A dermatoscopic image of a skin lesion.
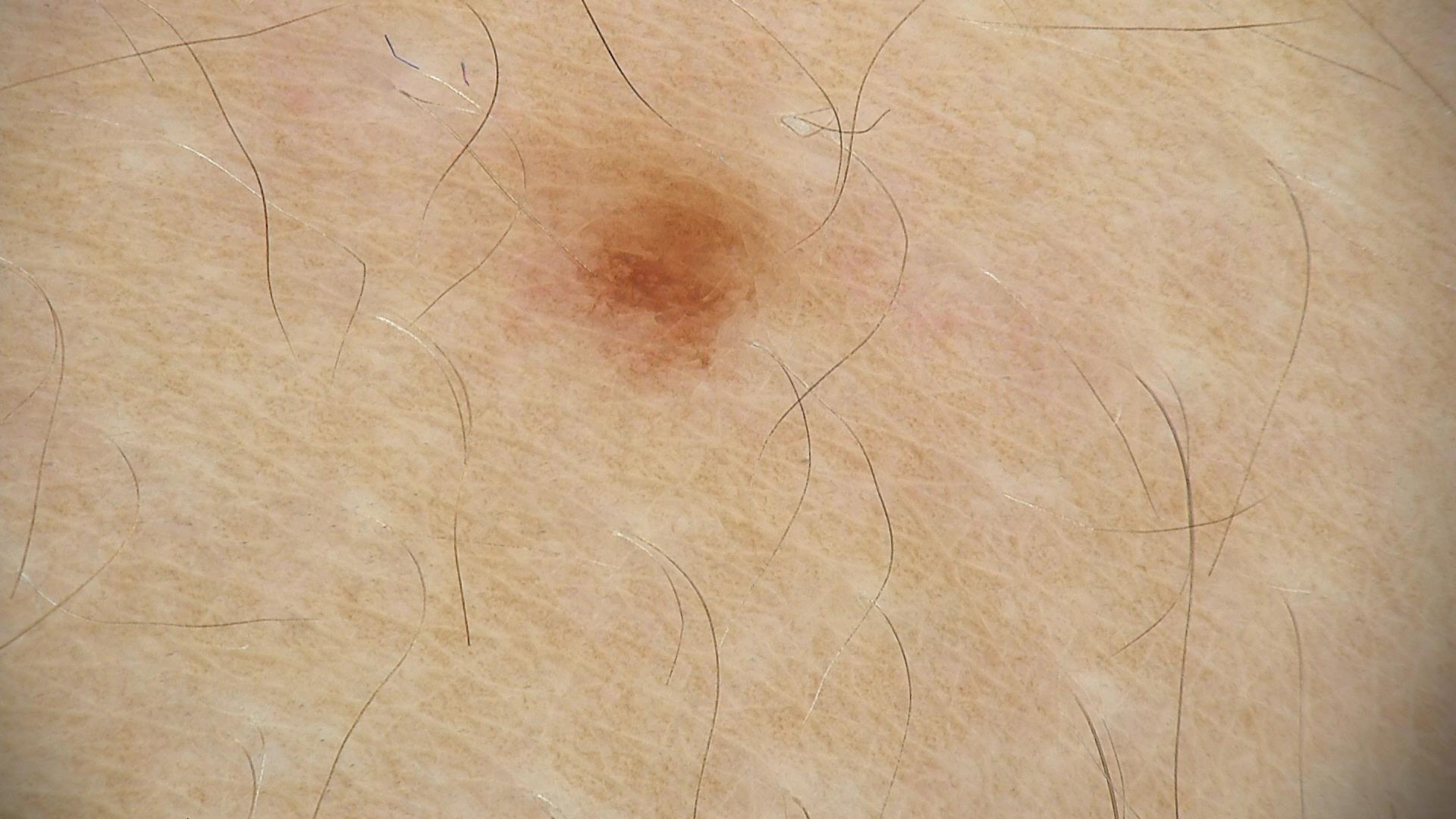assessment = dysplastic junctional nevus (expert consensus).